This is a close-up image.
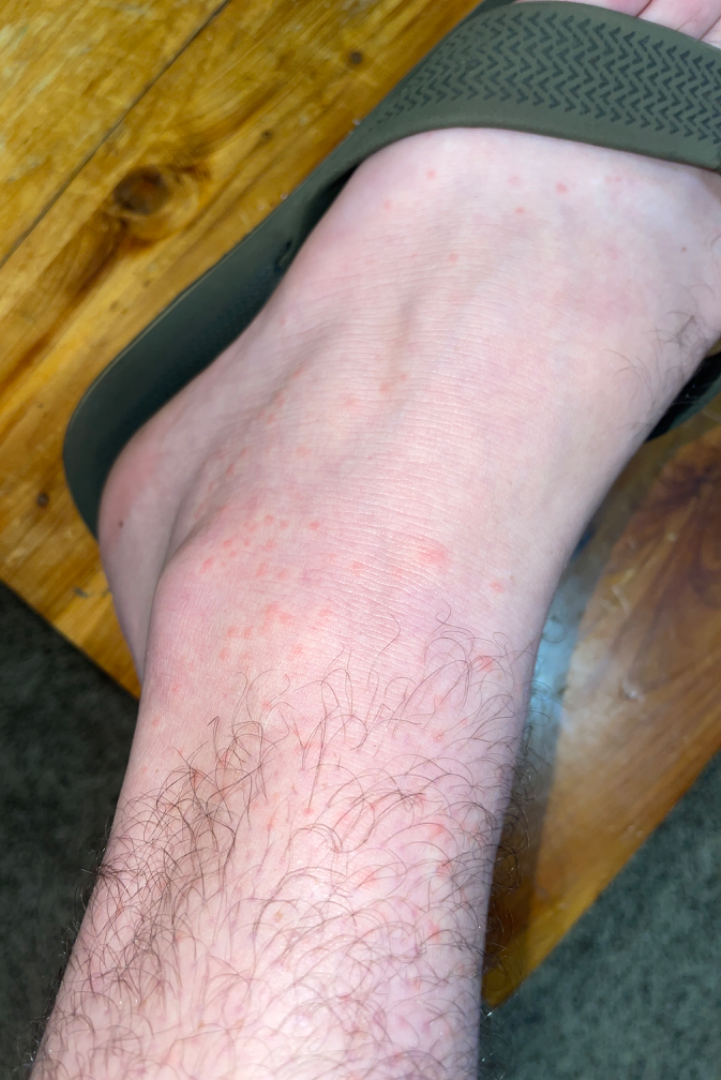Q: What conditions are considered?
A: the differential, in no particular order, includes Lichen planus/lichenoid eruption, Insect Bite and Allergic Contact Dermatitis